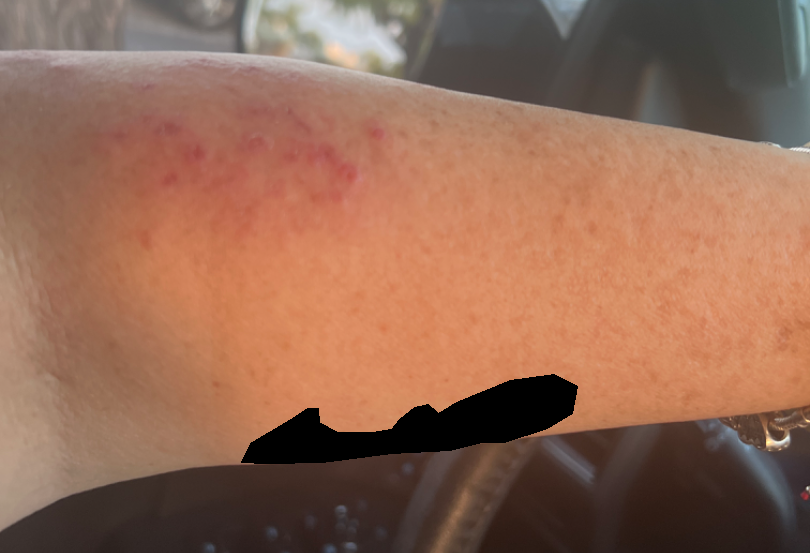<summary>
<patient_category>skin that appeared healthy to them</patient_category>
<texture>raised or bumpy</texture>
<body_site>leg, arm</body_site>
<shot_type>at an angle</shot_type>
<symptoms>itching, burning, pain</symptoms>
<differential>
  <tied_lead>Tinea, Insect Bite, Allergic Contact Dermatitis</tied_lead>
</differential>
</summary>